Male subject, age 18–29. The lesion is associated with burning. This image was taken at a distance. The patient described the issue as a rash. The lesion is described as raised or bumpy. Fitzpatrick skin type I. Present for about one day. No relevant systemic symptoms.
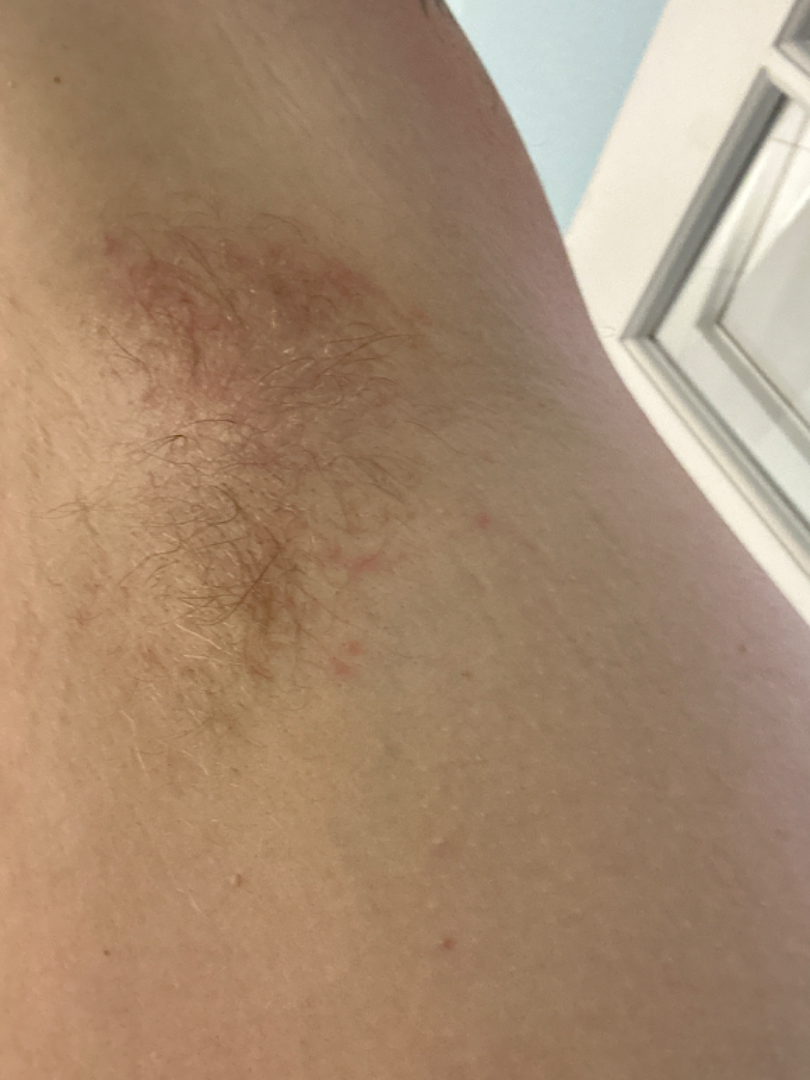{"differential": {"tied_lead": ["Intertrigo", "Seborrheic Dermatitis"], "unlikely": ["Folliculitis"]}}